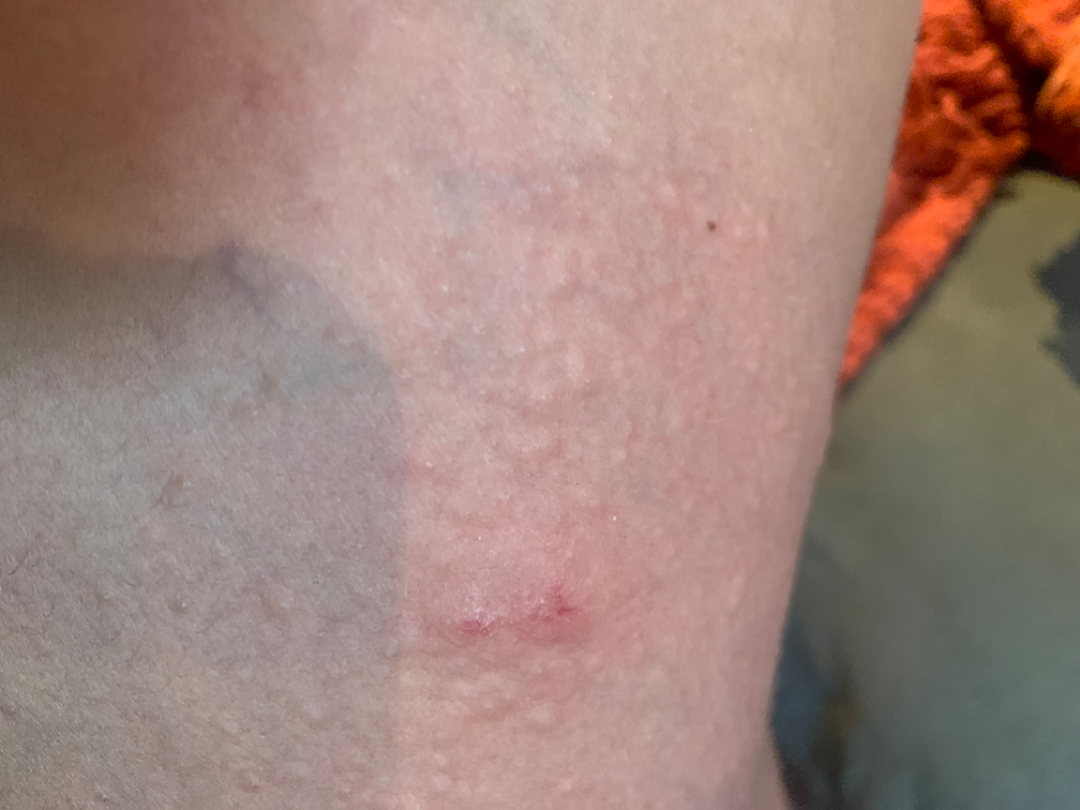assessment: could not be assessed | body site: leg | surface texture: raised or bumpy | skin tone: lay reviewers estimated Monk skin tone scale 2 (US pool) or 3 (India pool) | duration: less than one week | photo taken: close-up.